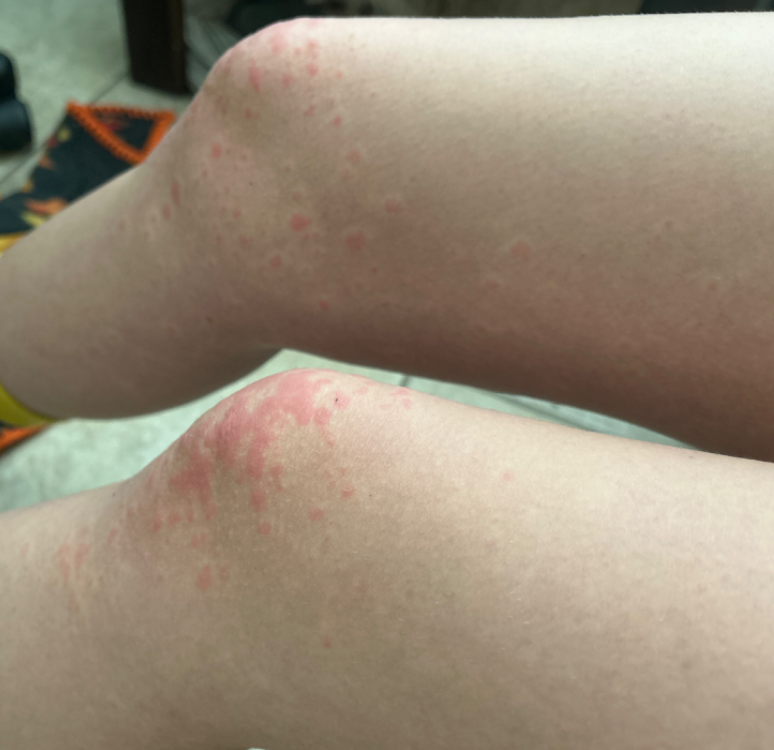Q: What is the differential diagnosis?
A: most consistent with Viral Exanthem